The affected area is the back of the torso, front of the torso and head or neck. The subject is a female aged 18–29. An image taken at an angle: 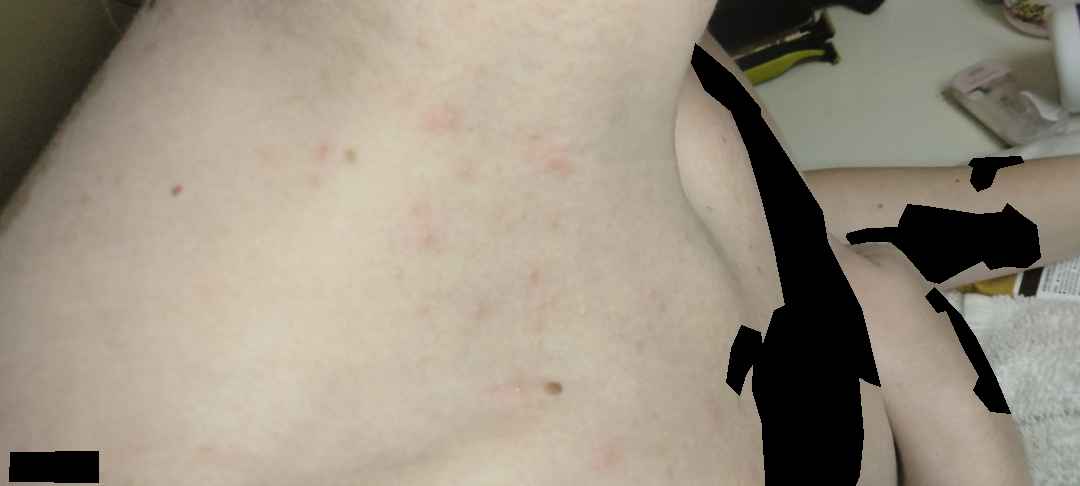differential diagnosis: Acne (55%); Folliculitis (27%); Allergic Contact Dermatitis (18%).